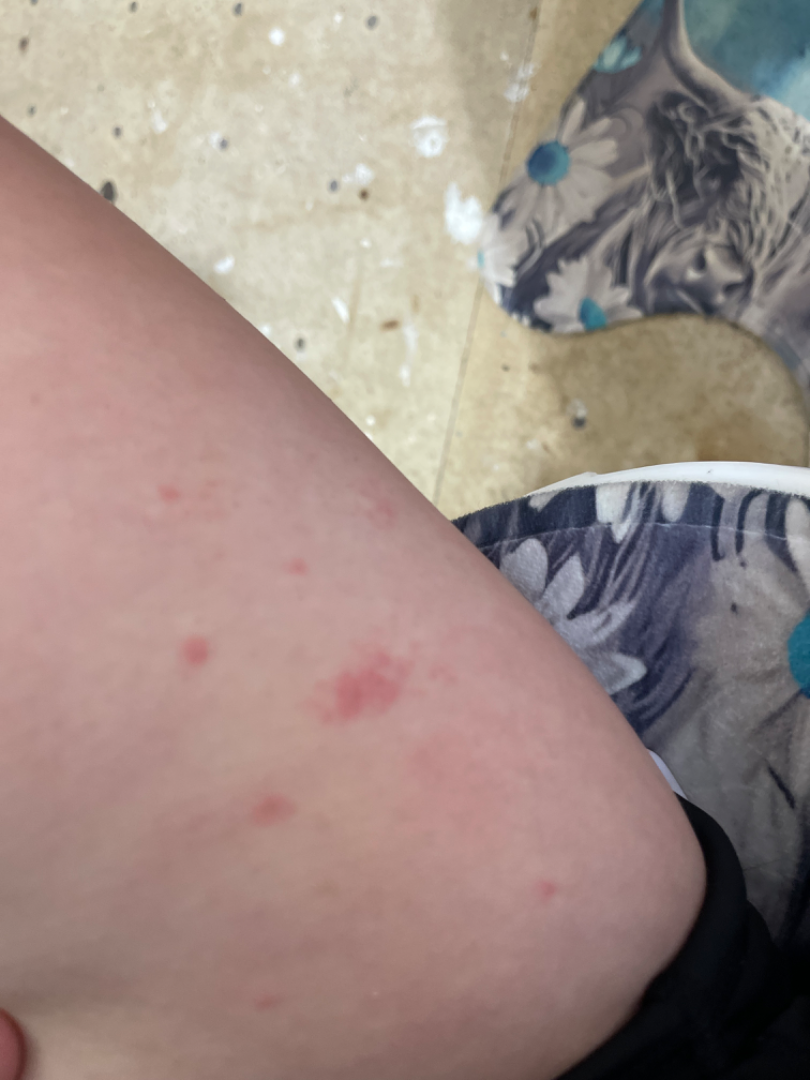Q: Image view?
A: at an angle
Q: Anatomic location?
A: leg
Q: What is the differential diagnosis?
A: Eczema (leading); Urticaria (possible)